A dermoscopy image of a single skin lesion:
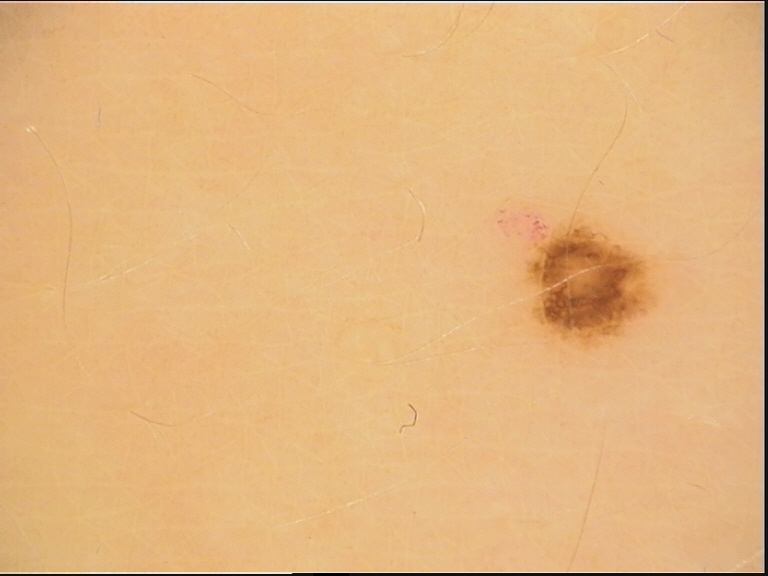diagnostic label: dysplastic junctional nevus (expert consensus).